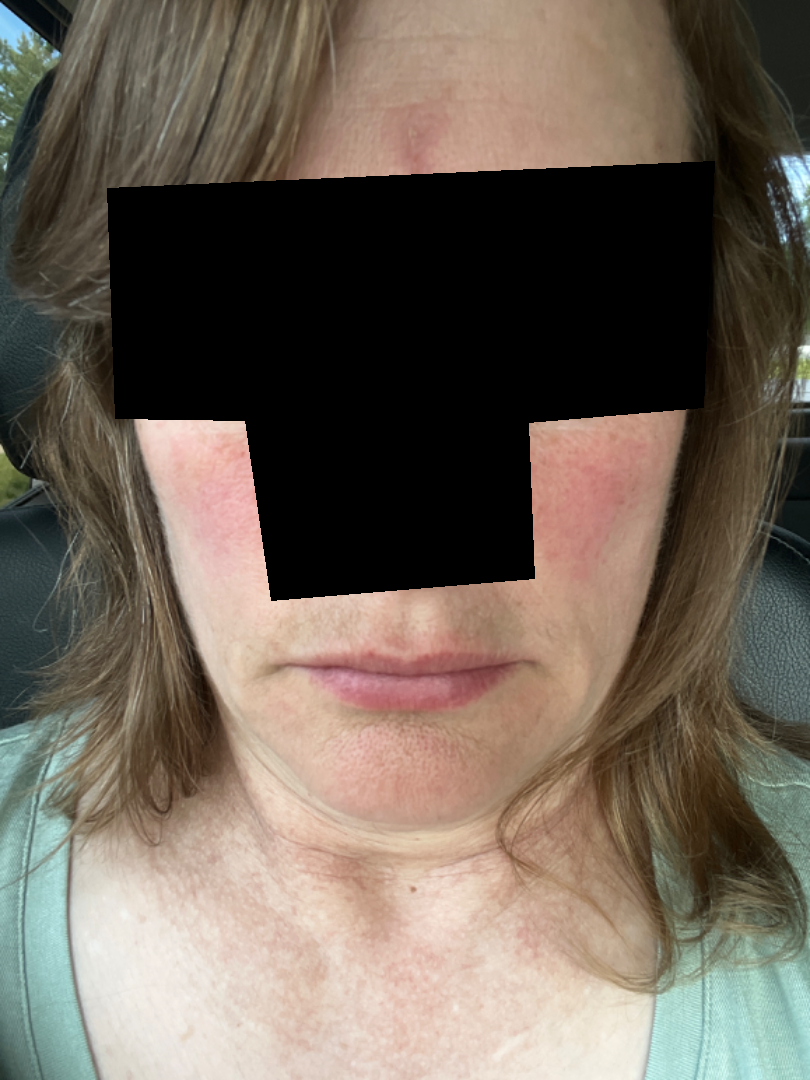The condition could not be reliably identified from the image. This image was taken at a distance.